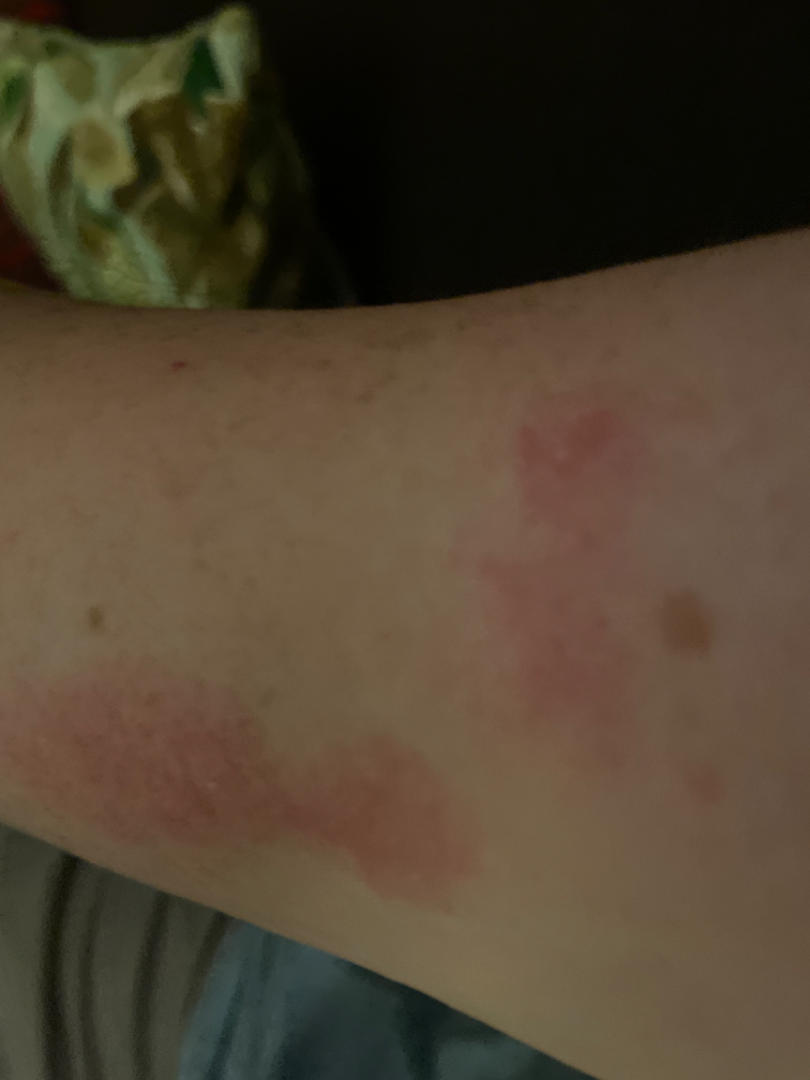{
  "assessment": "indeterminate from the photograph",
  "duration": "more than one year",
  "texture": "rough or flaky",
  "patient": "male, age 50–59",
  "body_site": [
    "front of the torso",
    "arm",
    "head or neck"
  ],
  "patient_category": "a rash",
  "shot_type": "close-up",
  "symptoms": [
    "bothersome appearance",
    "itching"
  ]
}